The patient is a male aged 30–39; the arm is involved; the photograph is a close-up of the affected area — 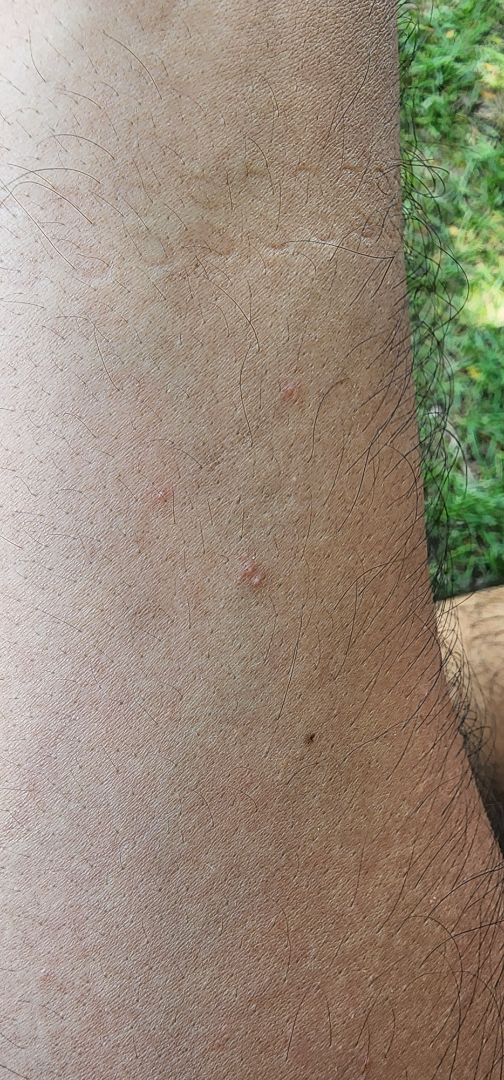Case summary:
– dermatologist impression — Insect Bite (considered); Folliculitis (considered)